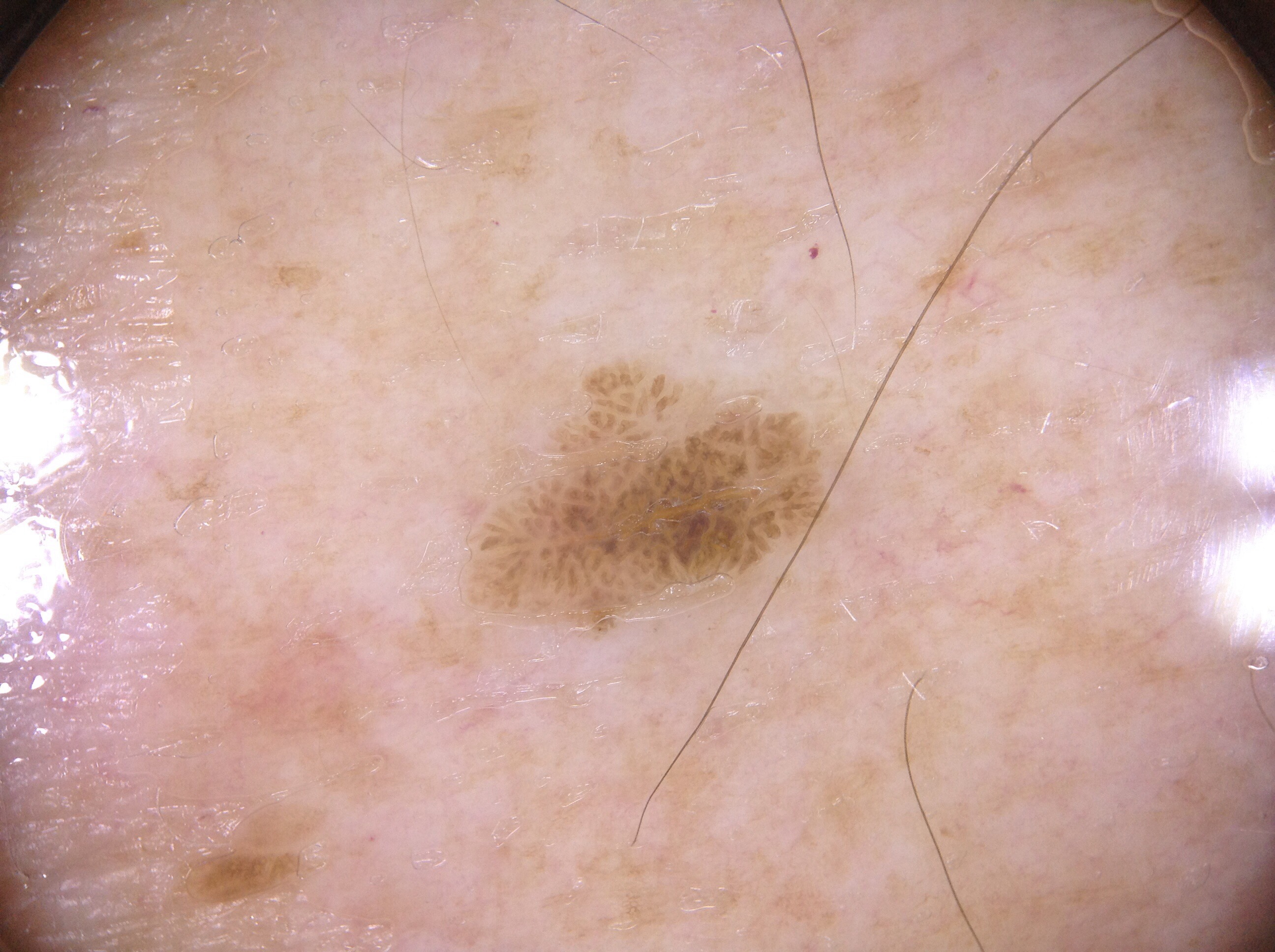Case summary: A skin lesion imaged with a dermatoscope. A male patient roughly 75 years of age. As (left, top, right, bottom), the lesion occupies the region [488, 380, 827, 617]. Dermoscopically, the lesion shows no streaks, negative network, milia-like cysts, or pigment network. The lesion covers approximately 4% of the dermoscopic field. Assessment: Clinically diagnosed as a seborrheic keratosis, a lesion of keratinocytic origin.